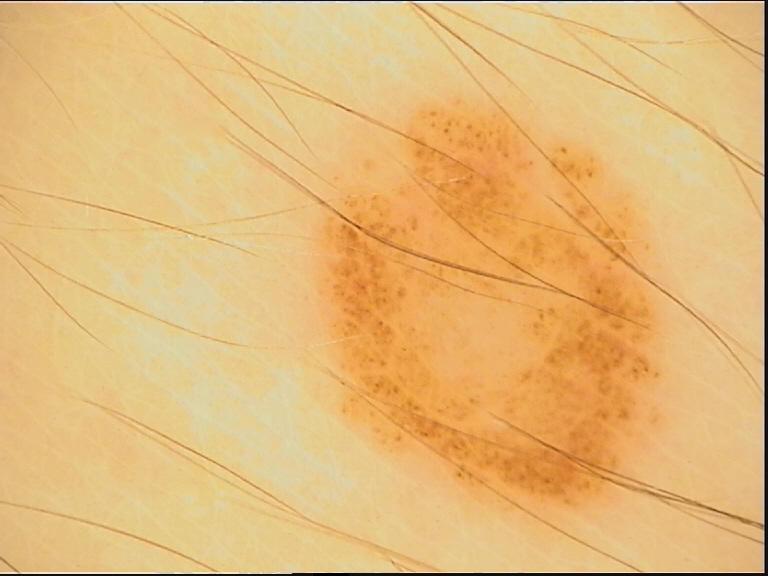The diagnostic label was a dysplastic junctional nevus.